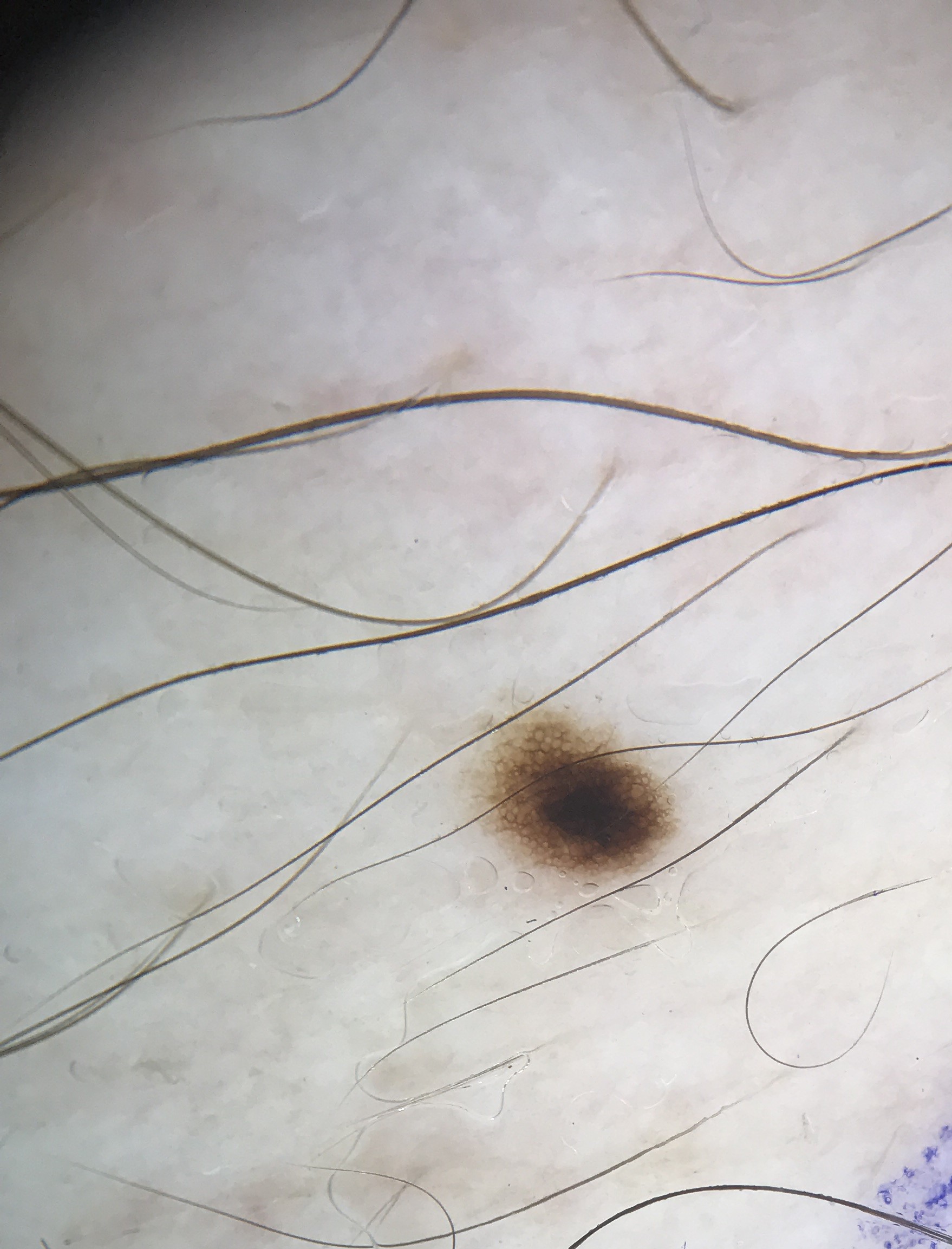A dermoscopic photograph of a skin lesion.
Classified as a banal lesion — a junctional nevus.